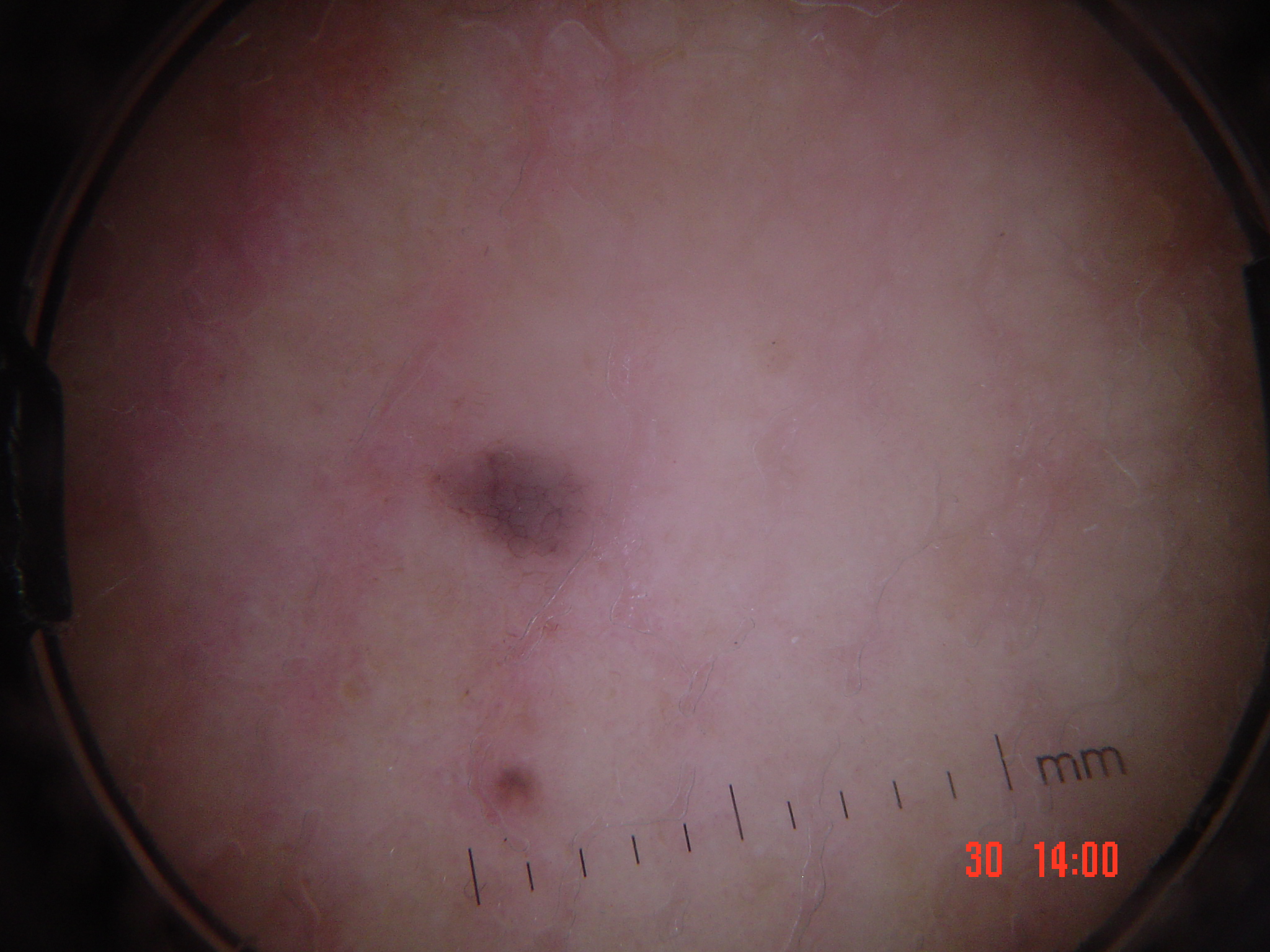A dermoscopic image of a skin lesion. Labeled as a keratinocytic lesion — a seborrheic keratosis.